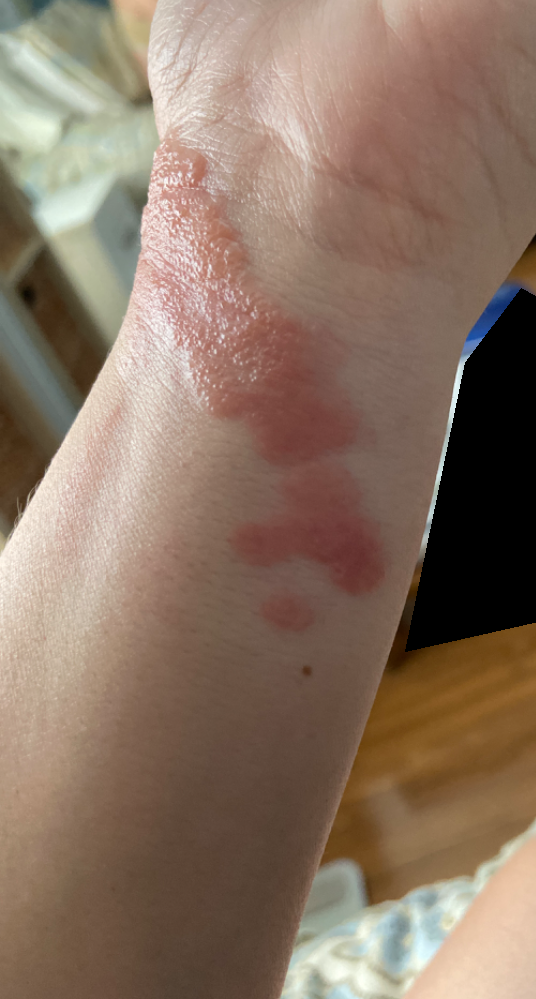Review: Favoring Allergic Contact Dermatitis; with consideration of Linear IgA disease.